A dermoscopic photograph of a skin lesion.
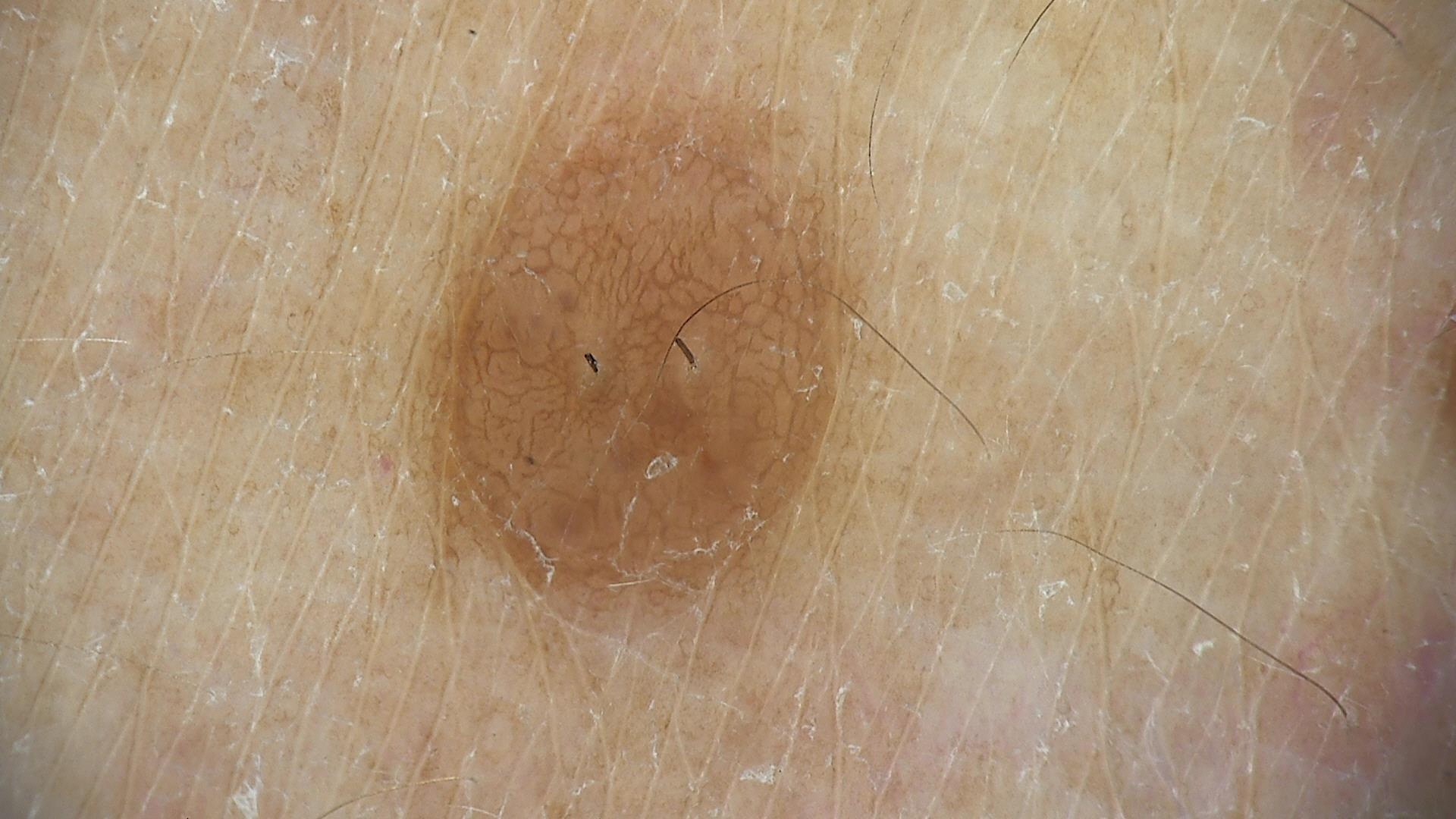Classified as a banal lesion — a dermal nevus.